Female patient, age 30–39. This is a close-up image. The affected area is the arm:
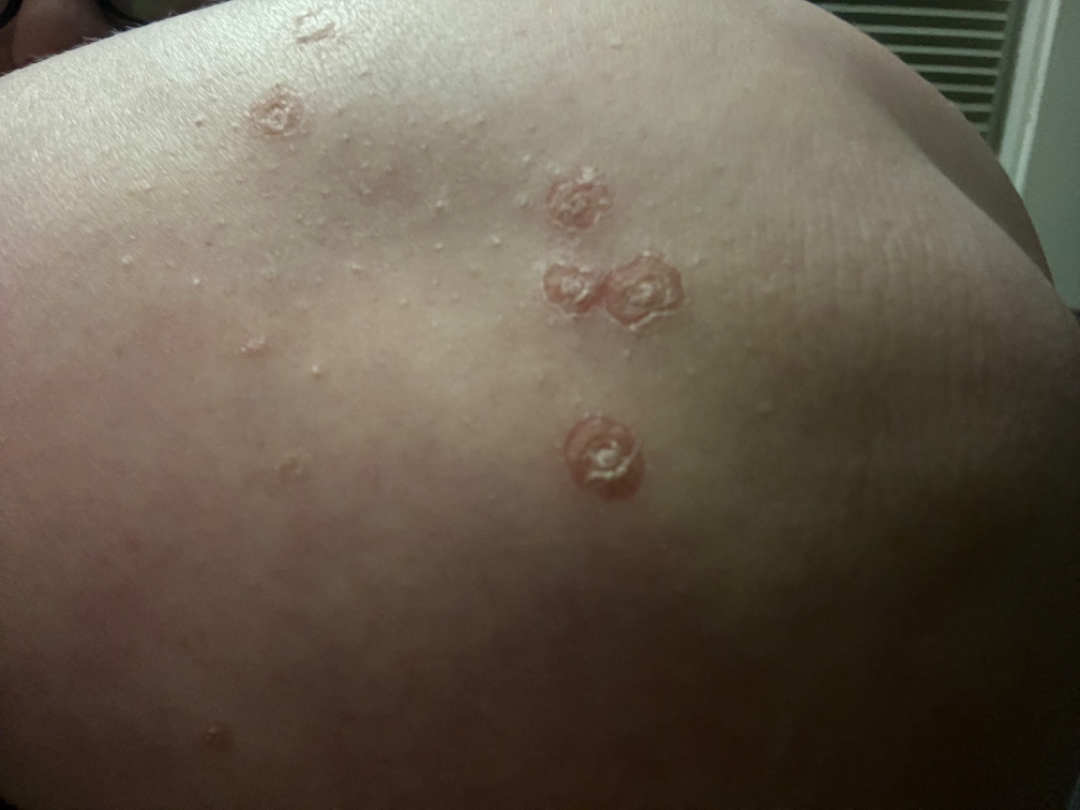On dermatologist assessment of the image, most likely Psoriasis; also raised was Skin infection; also consider Eczema.